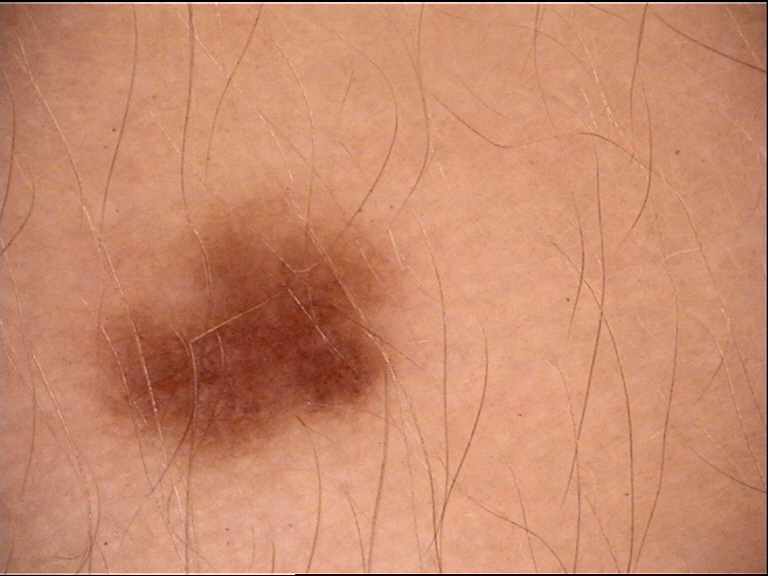image: dermatoscopy
diagnosis:
  name: dysplastic junctional nevus
  code: jd
  malignancy: benign
  super_class: melanocytic
  confirmation: expert consensus